Located on the arm; a close-up photograph:
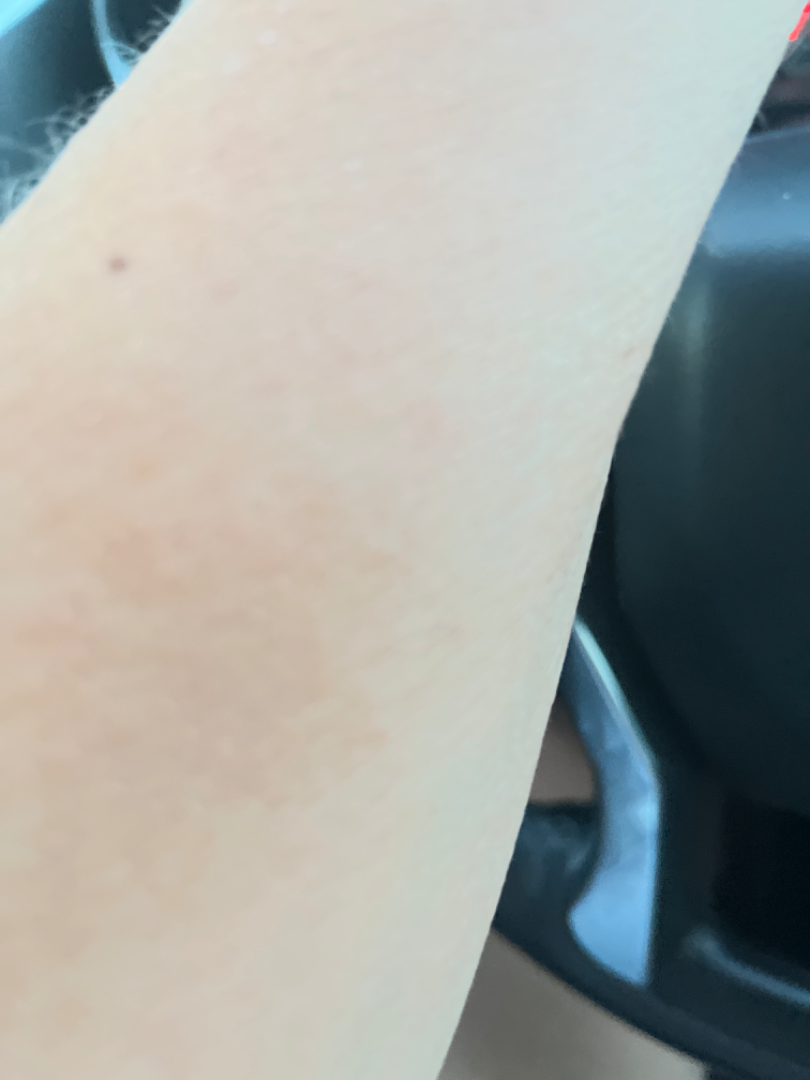<report>
<assessment>indeterminate</assessment>
</report>